The patient indicates the condition has been present for three to twelve months · a close-up photograph · the patient considered this skin that appeared healthy to them · the patient also reports shortness of breath and fatigue · the patient is female · the lesion involves the top or side of the foot and sole of the foot · Fitzpatrick phototype II · reported lesion symptoms include itching, pain, burning and bothersome appearance · the lesion is described as fluid-filled, rough or flaky and raised or bumpy: 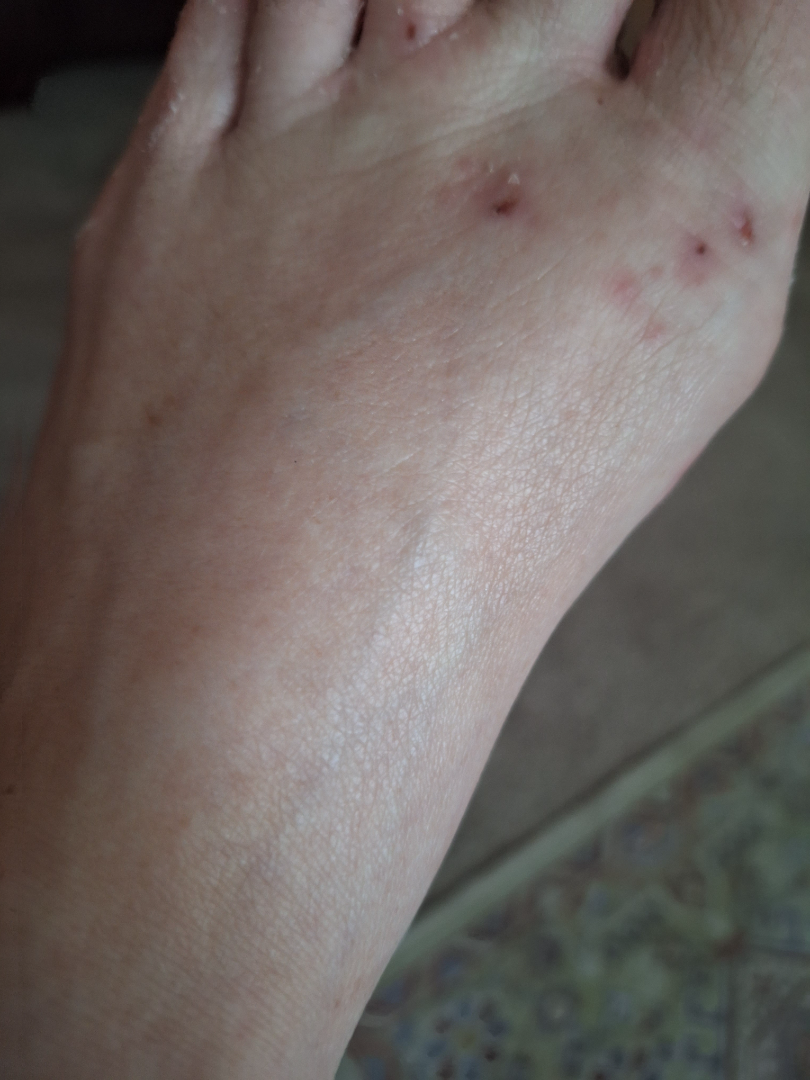On remote dermatologist review, Tinea (leading); Eczema (considered); Irritant Contact Dermatitis (unlikely).